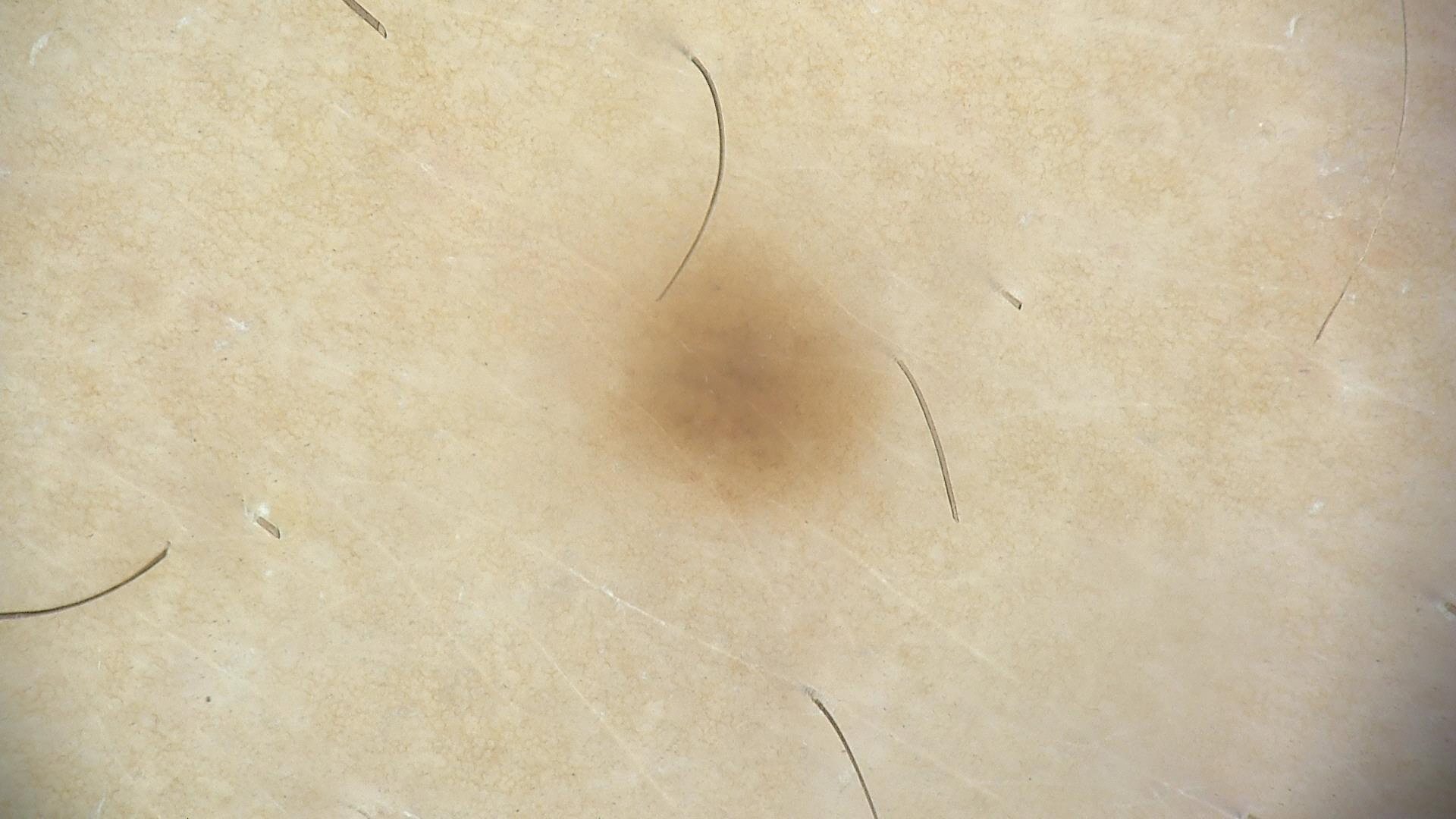image — dermatoscopy
assessment — dysplastic junctional nevus (expert consensus)